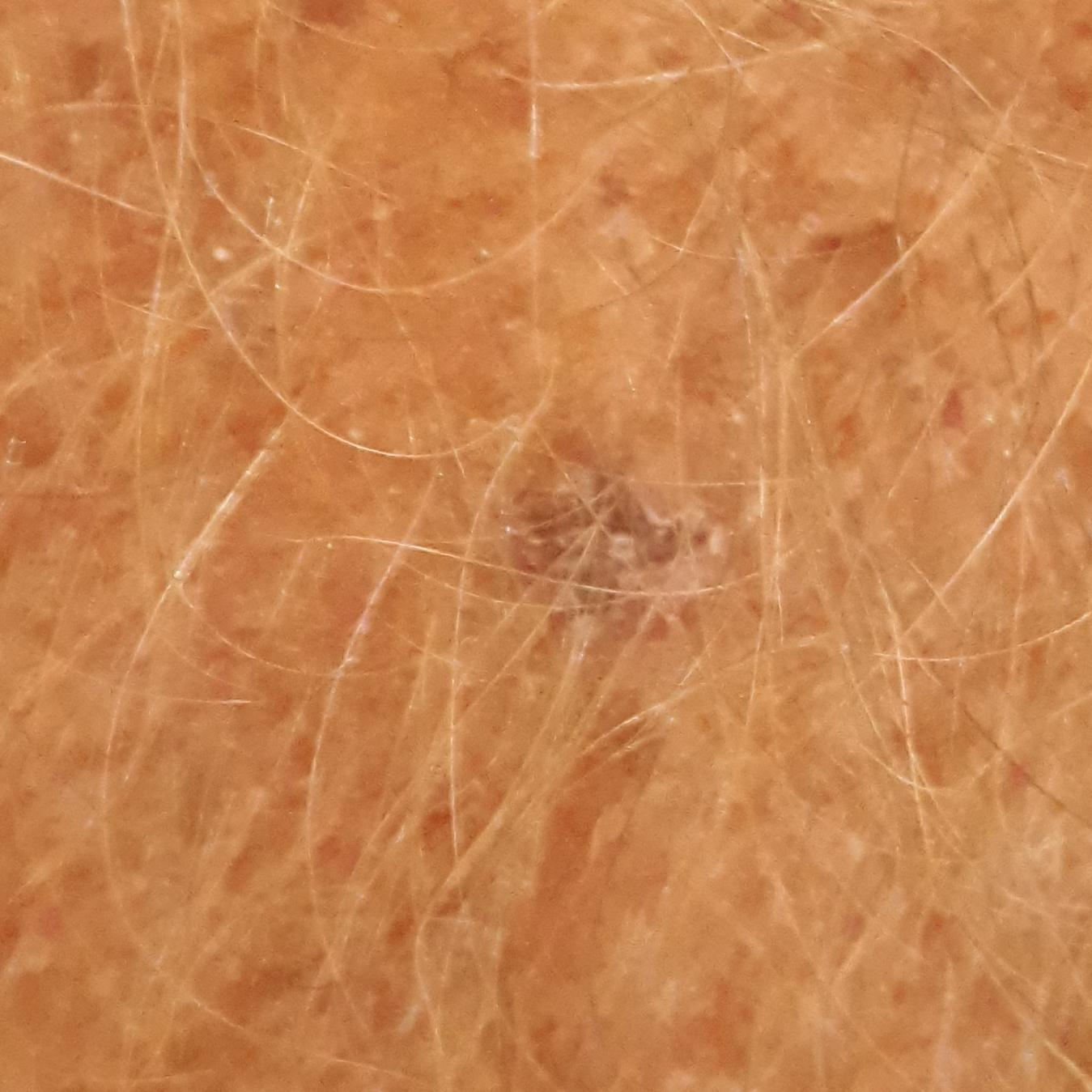Q: What is the imaging modality?
A: clinical photograph
Q: What is the diagnosis?
A: actinic keratosis (clinical consensus)